This is a close-up image: 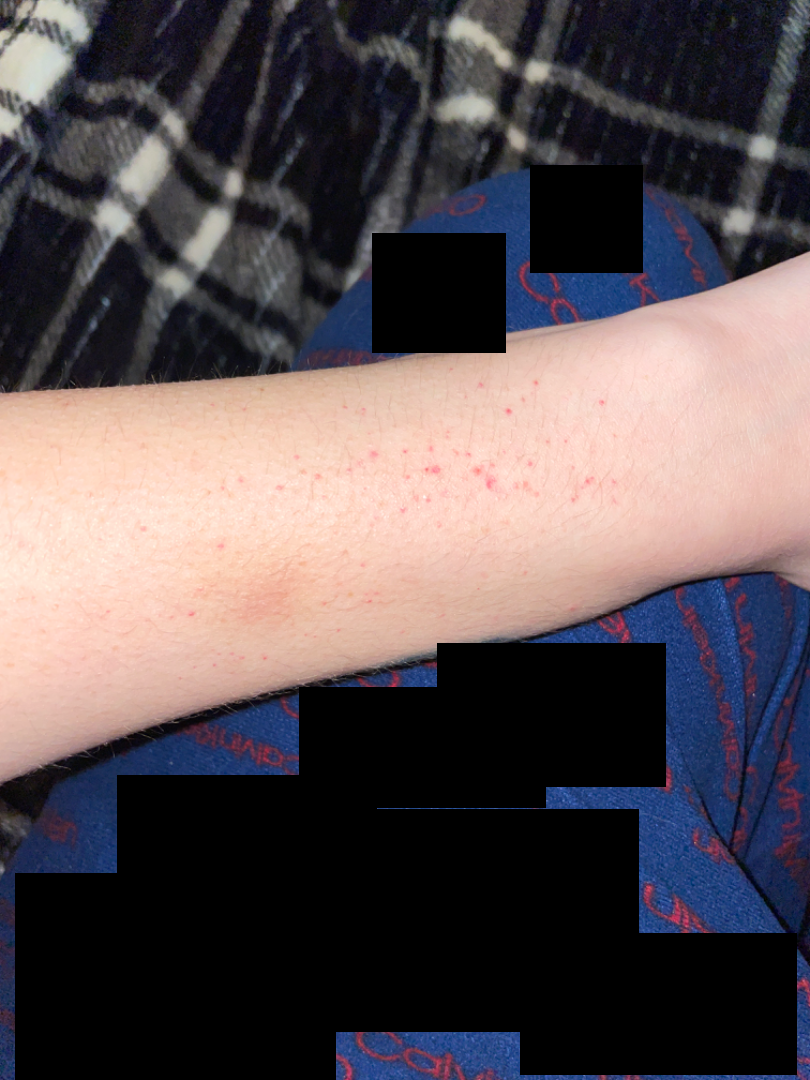{"differential": {"petechiae": 0.54, "Pigmented purpuric eruption": 0.23, "Leukocytoclastic Vasculitis": 0.23}}